A dermoscopic close-up of a skin lesion; a male subject, aged 48-52: 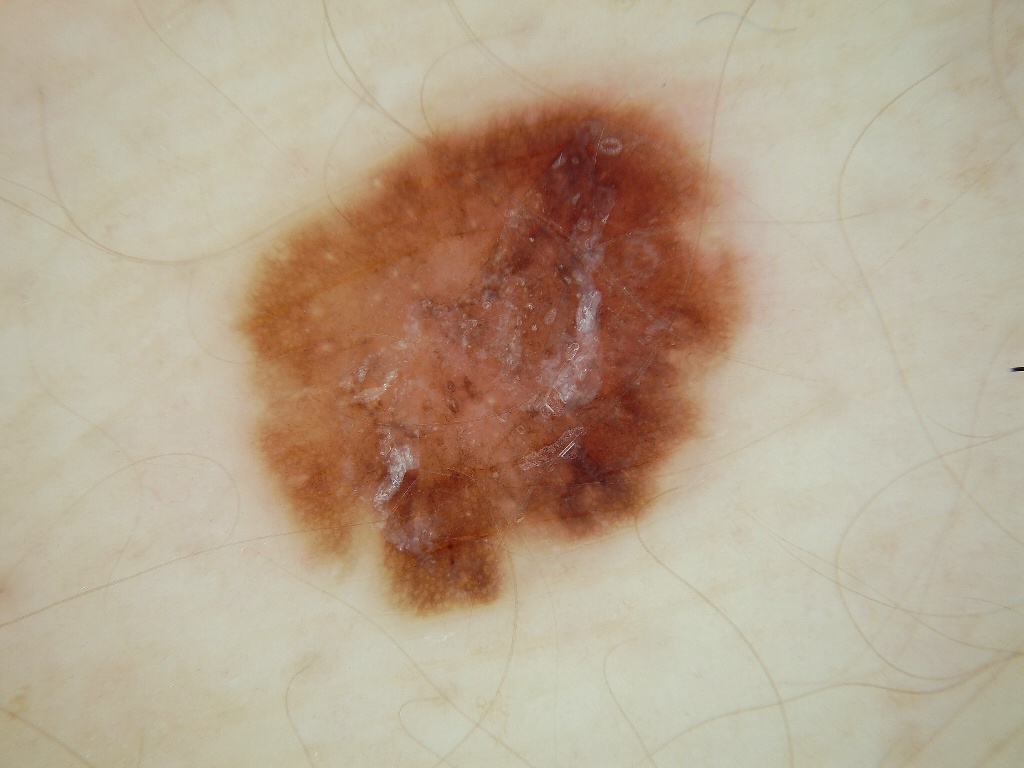Case summary:
• dermoscopic features — pigment network and milia-like cysts; absent: negative network, streaks, and globules
• lesion location — left=228, top=70, right=754, bottom=617
• assessment — a melanoma, a malignancy